The patient says their skin reddens with sun exposure: 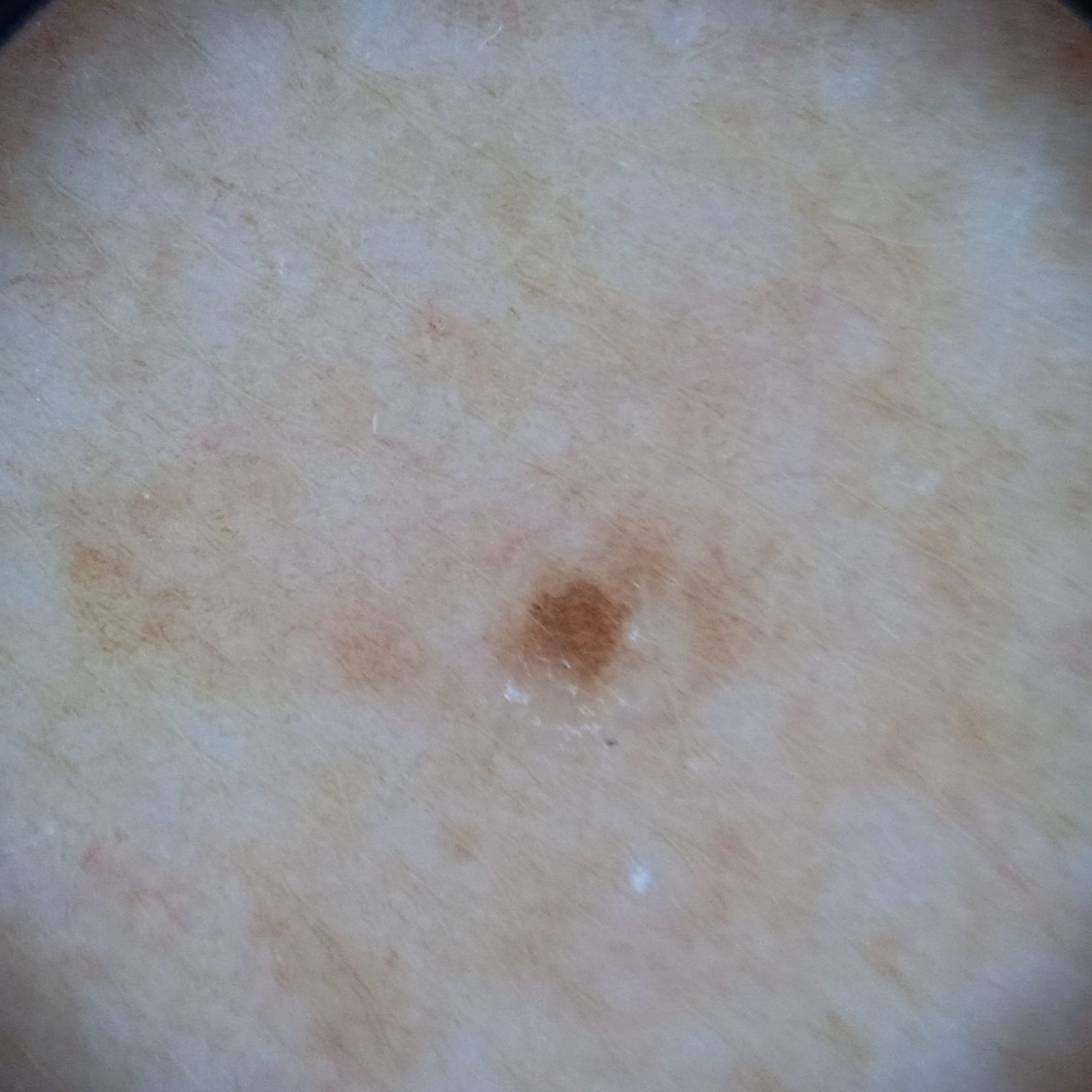Q: How large is the lesion?
A: 1.3 mm
Q: What was the diagnosis?
A: melanocytic nevus (dermatologist consensus)